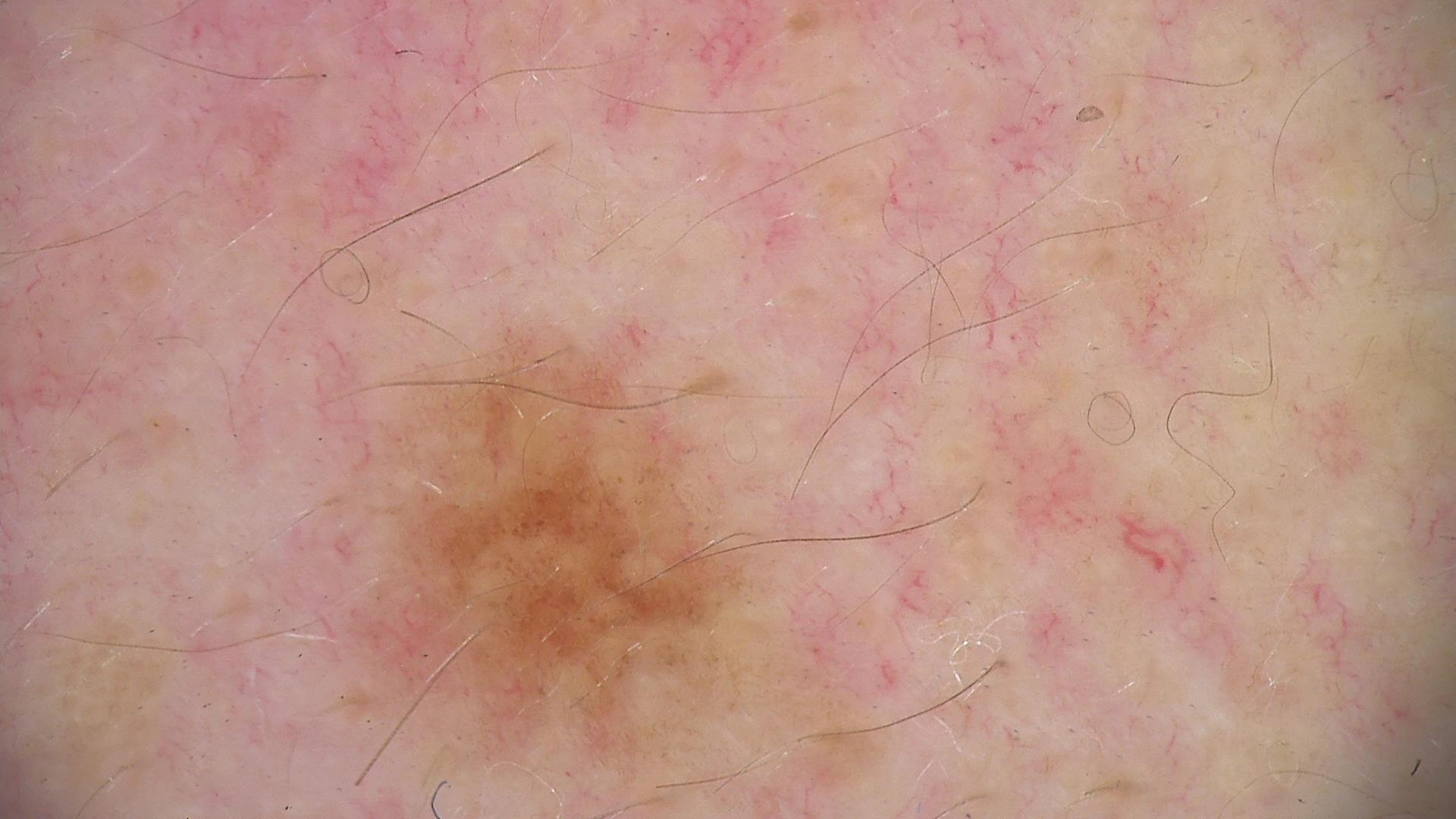{
  "image": "dermoscopy",
  "diagnosis": {
    "name": "dysplastic junctional nevus",
    "code": "jd",
    "malignancy": "benign",
    "super_class": "melanocytic",
    "confirmation": "expert consensus"
  }
}